The photograph is a close-up of the affected area, the contributor is a female aged 40–49, located on the front of the torso — 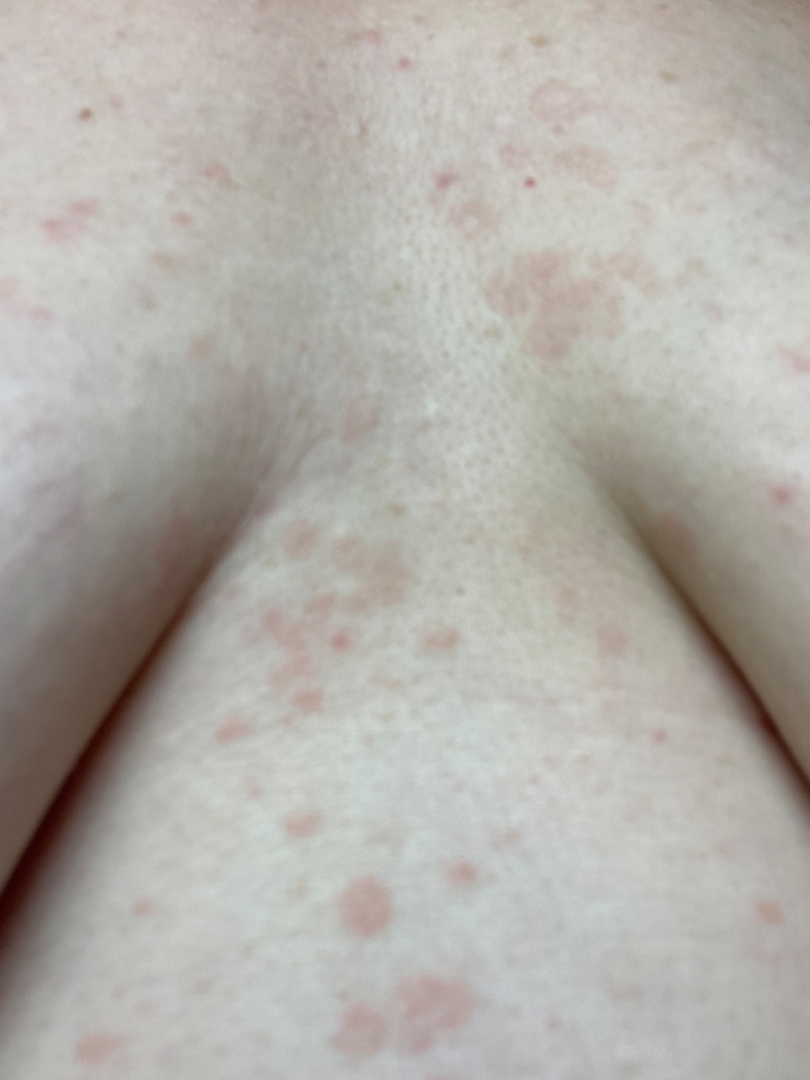Patient information:
The contributor reports the condition has been present for one to three months. The contributor reports the lesion is raised or bumpy and flat. The lesion is associated with bothersome appearance.
Review:
Most likely Tinea Versicolor; also raised was Pityriasis rosea; an alternative is Eczema.